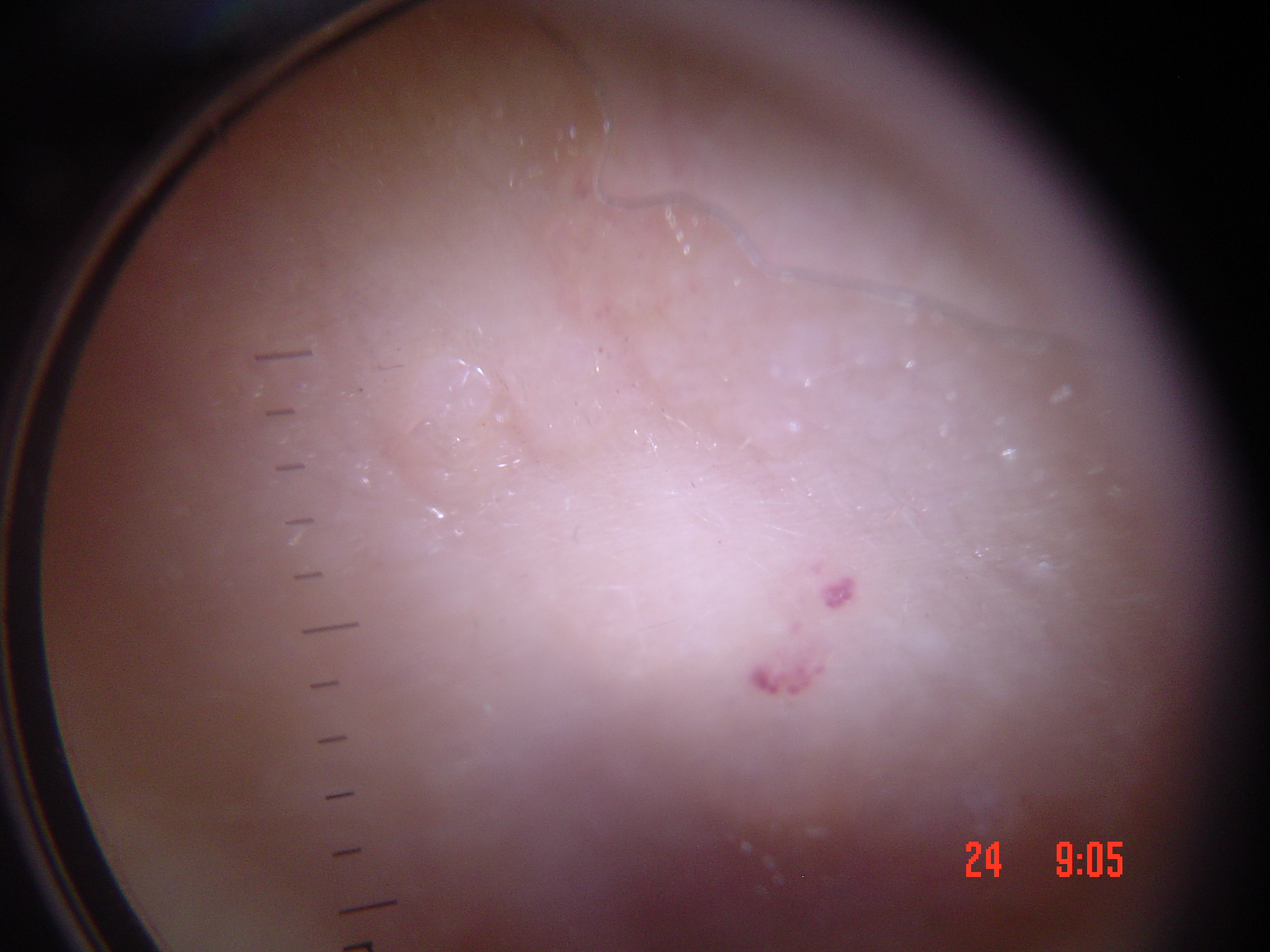A dermoscopic image of a skin lesion. The diagnosis was a vascular lesion — a hemangioma.